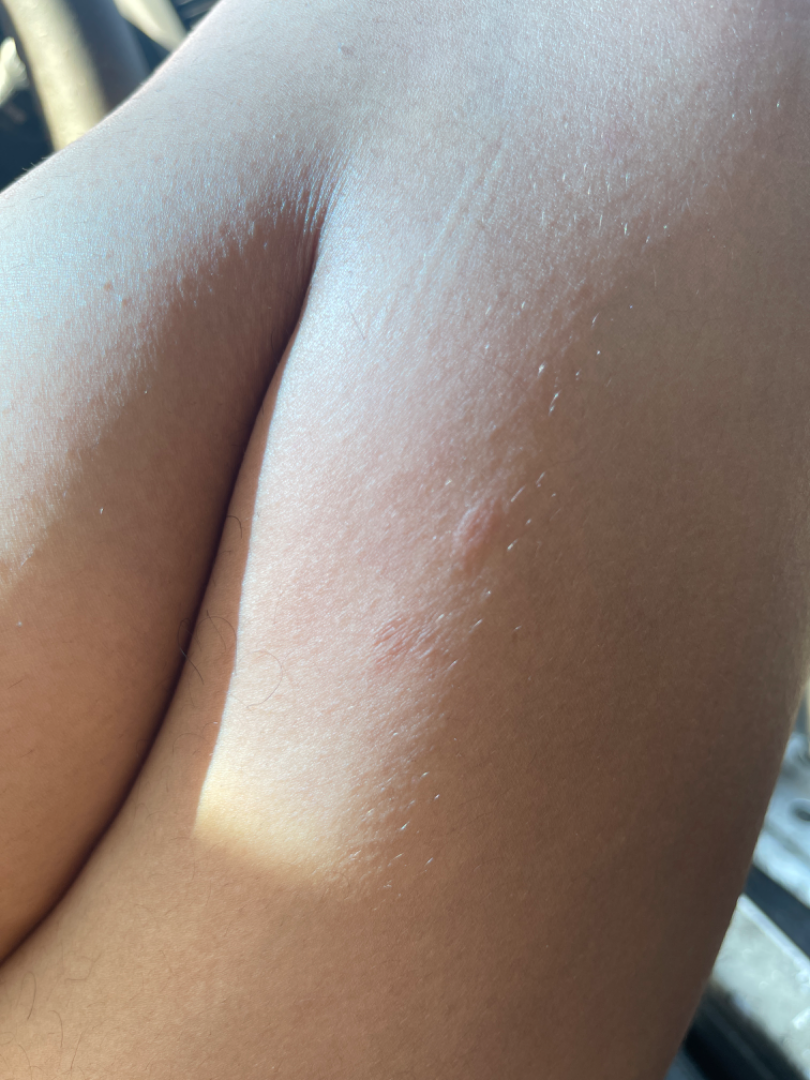assessment: could not be assessed
skin tone: Fitzpatrick skin type I; non-clinician graders estimated Monk skin tone scale 1 or 2 (two reviewer pools)
shot type: close-up